A female subject aged 68-72.
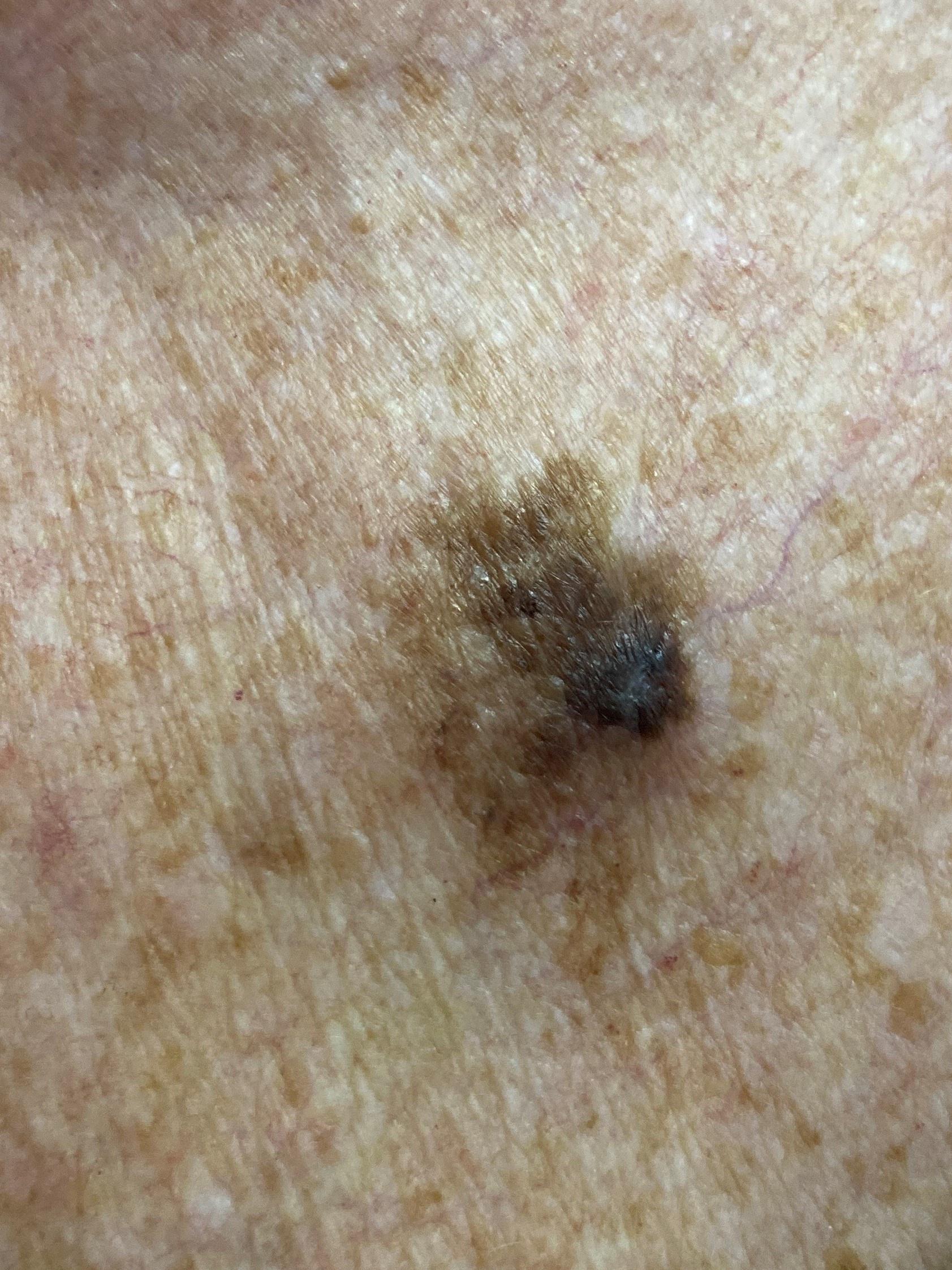Q: What is the diagnosis?
A: Melanoma (biopsy-proven)